Dermoscopy of a skin lesion: 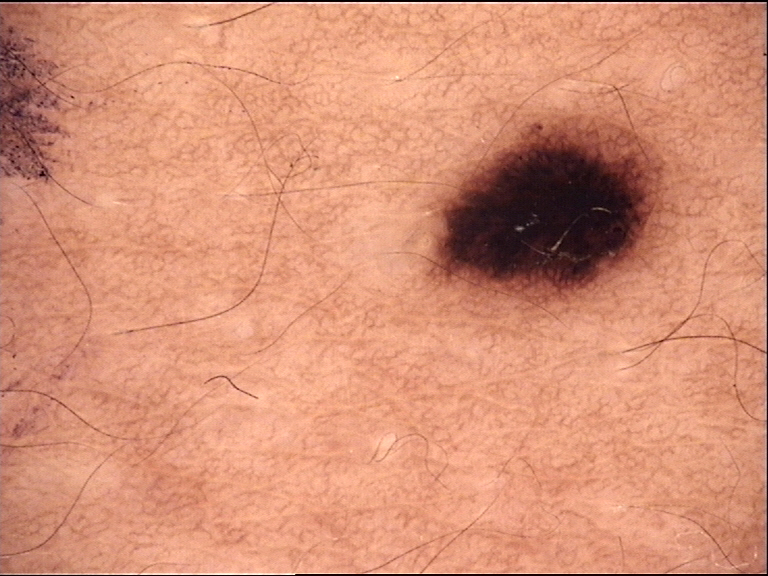Diagnosed as a banal lesion — a junctional nevus.